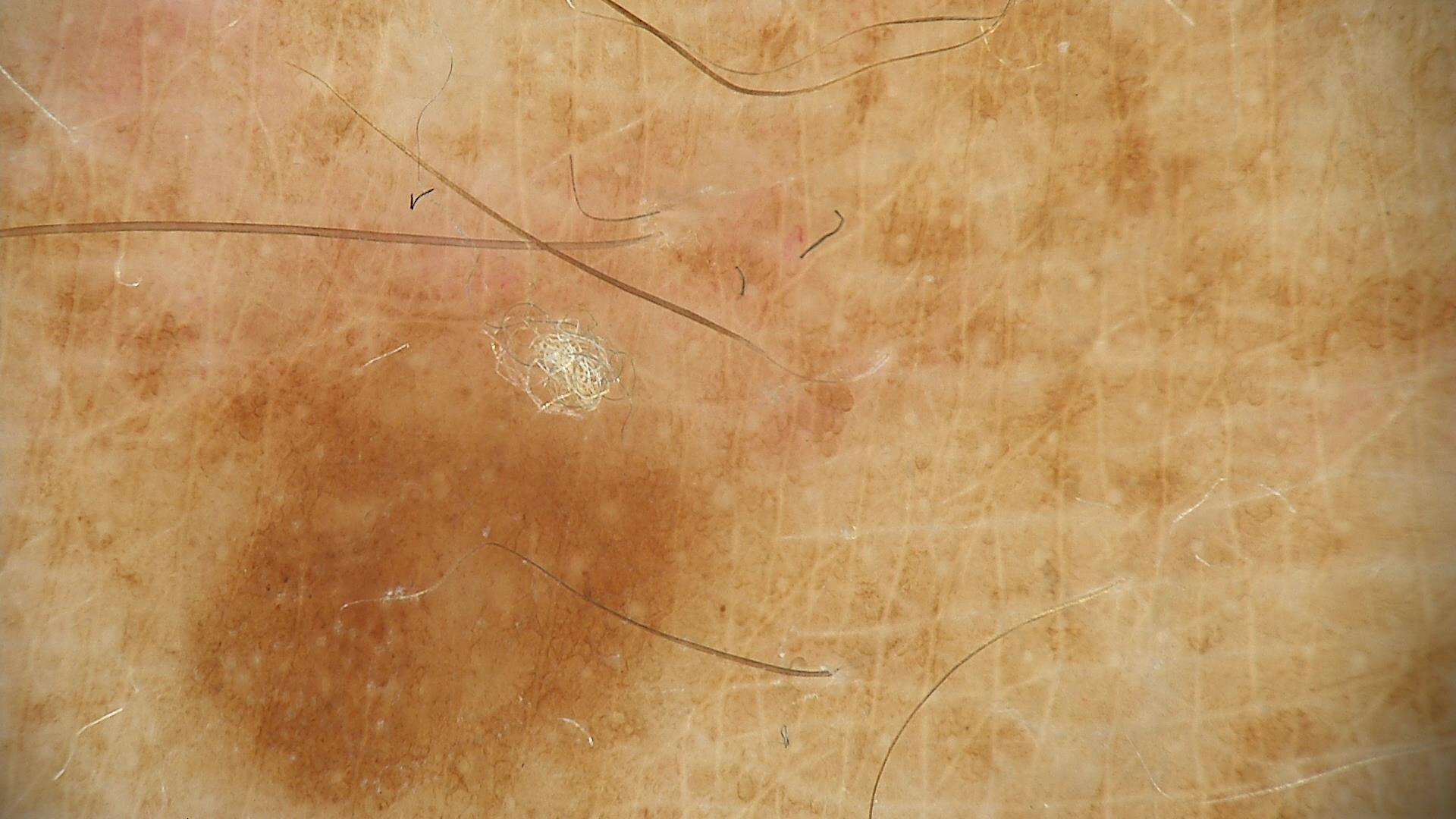A dermatoscopic image of a skin lesion. The diagnostic label was a dysplastic junctional nevus.